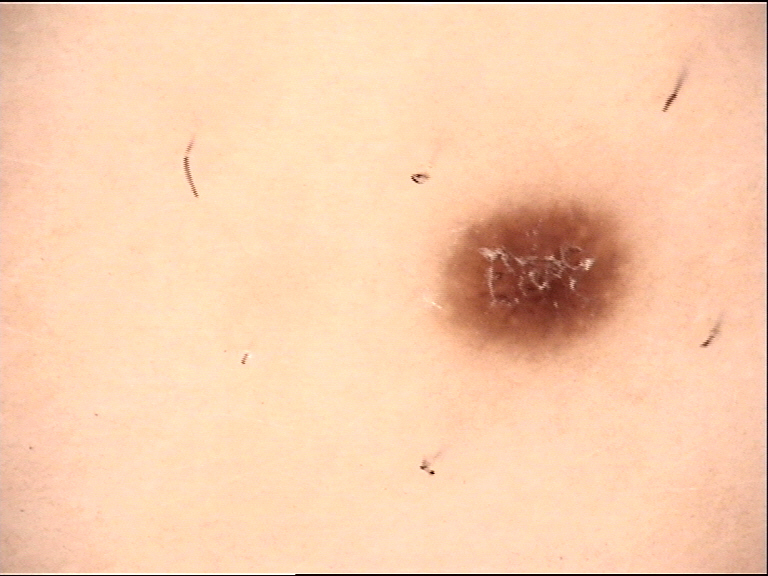Case: A dermoscopic close-up of a skin lesion. Impression: The diagnostic label was a dysplastic junctional nevus.